A dermatoscopic image of a skin lesion: 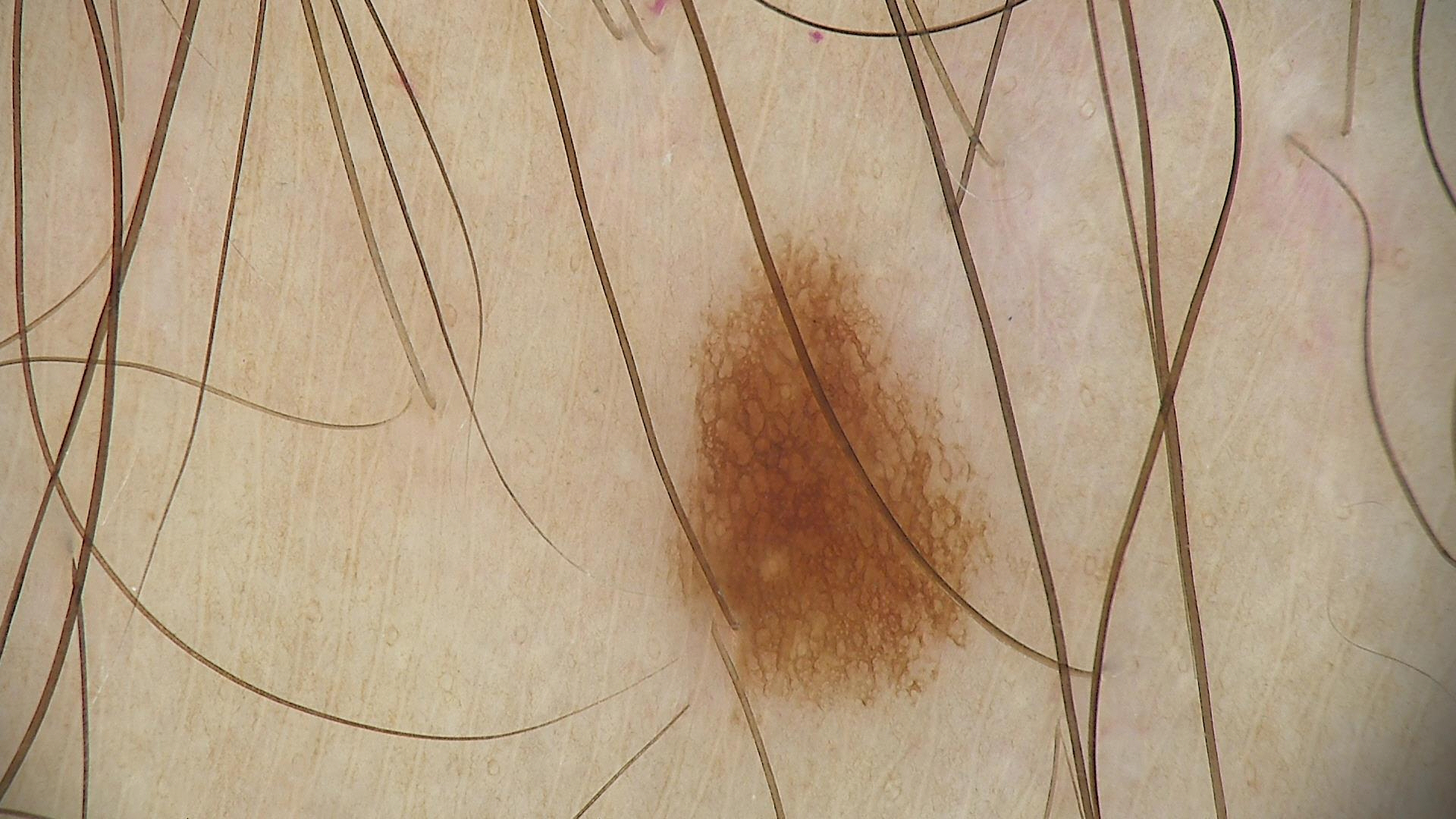Case:
- diagnosis · junctional nevus (expert consensus)